A female subject 15 years of age; a skin lesion imaged with a dermatoscope; collected as part of a research study, without a referral diagnosis.
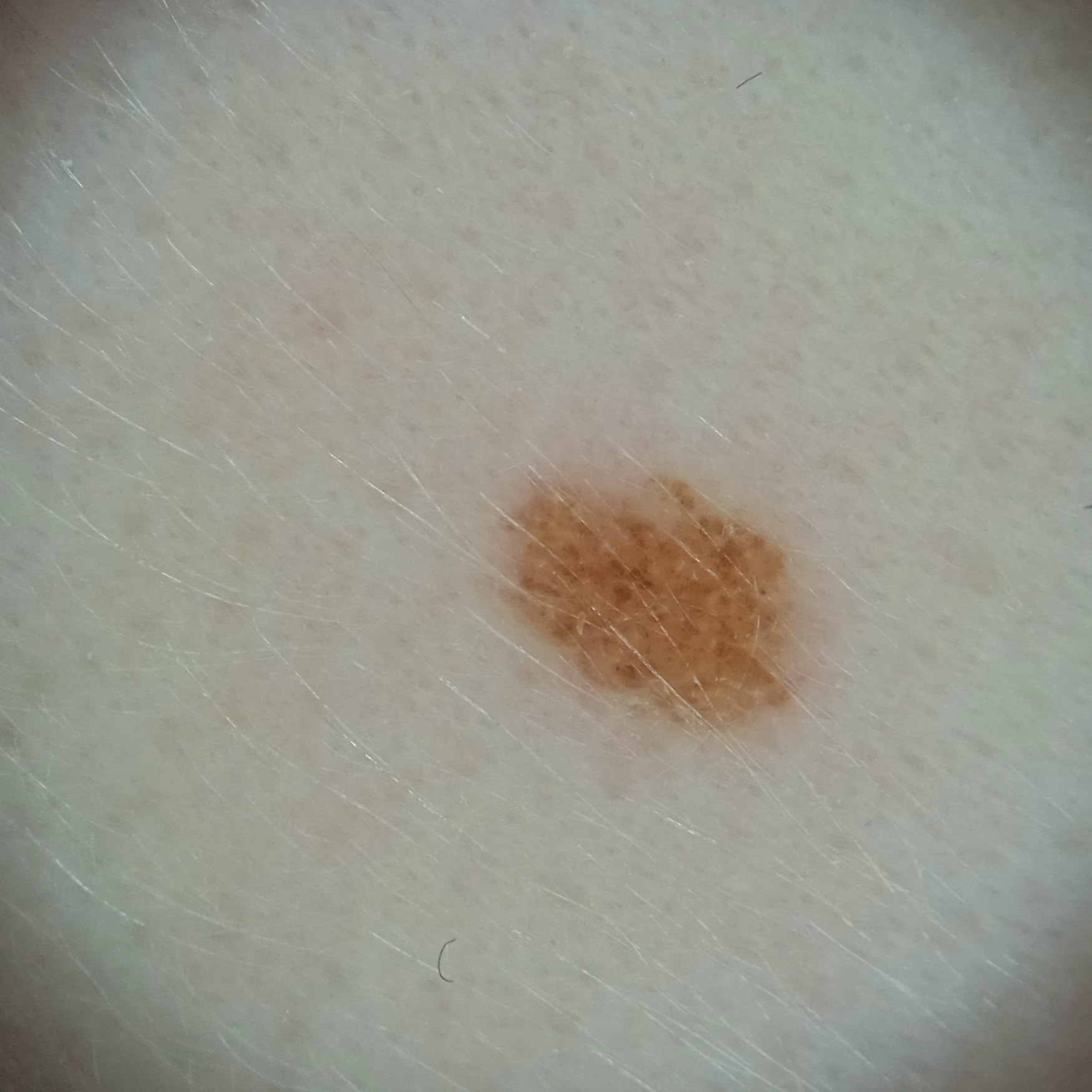The lesion involves the face. The lesion measures approximately 3.6 mm. The dermatologists' assessment was a melanocytic nevus.